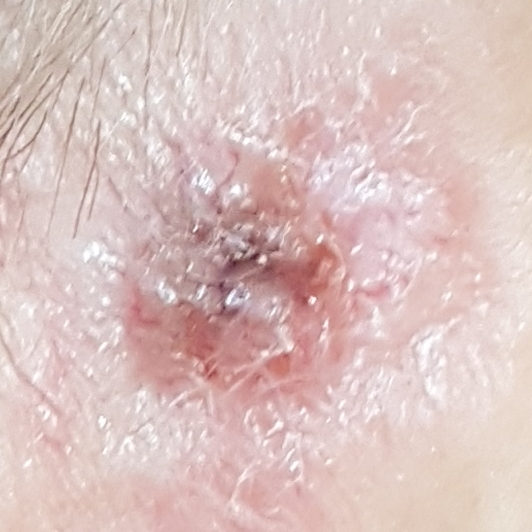- imaging: clinical photo
- patient: female, age 70
- anatomic site: an ear
- diagnostic label: basal cell carcinoma (biopsy-proven)